A skin lesion imaged with a dermatoscope.
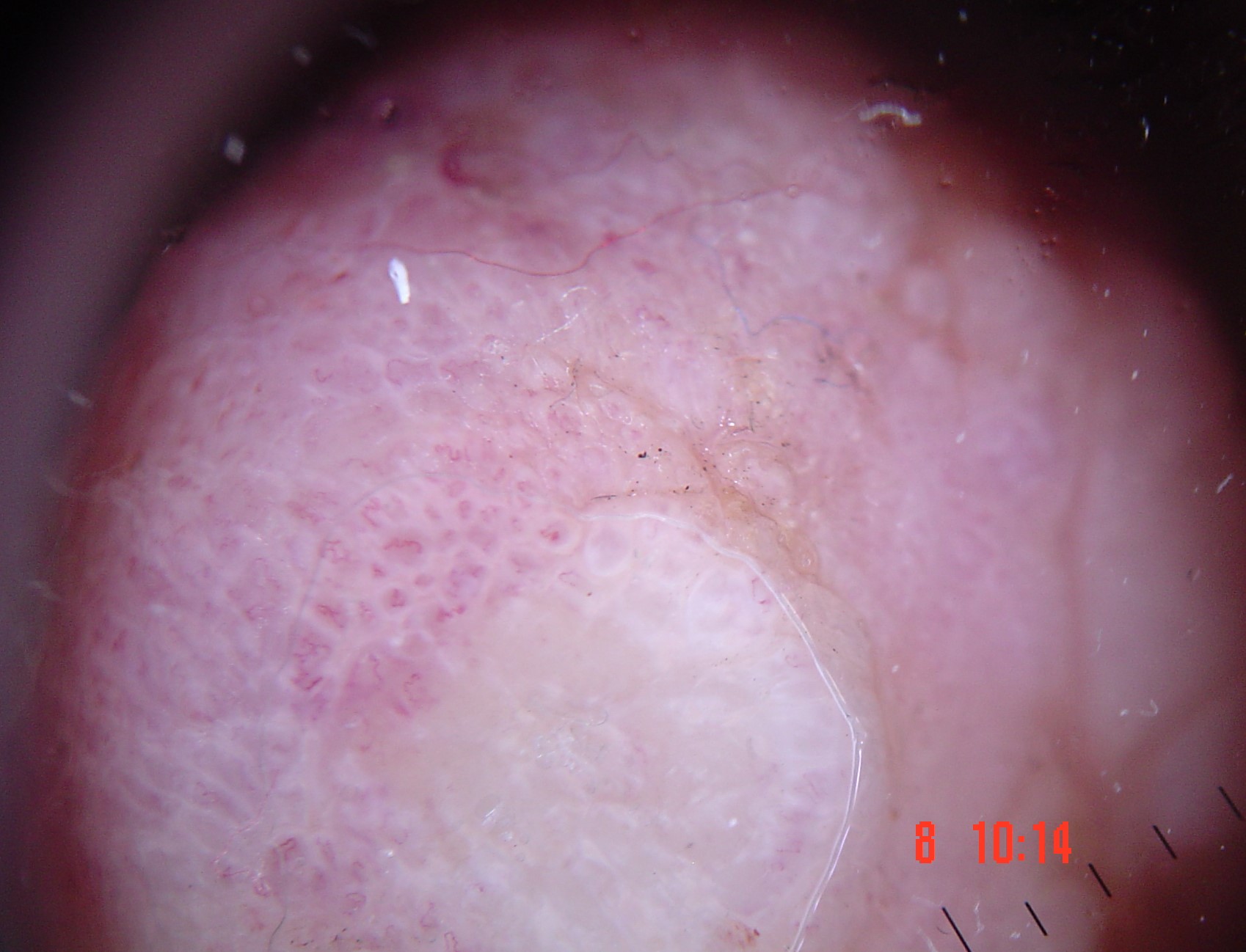diagnosis:
  name: acral nodular melanoma
  code: anm
  malignancy: malignant
  super_class: melanocytic
  confirmation: histopathology